A female patient approximately 65 years of age · a dermoscopic close-up of a skin lesion:
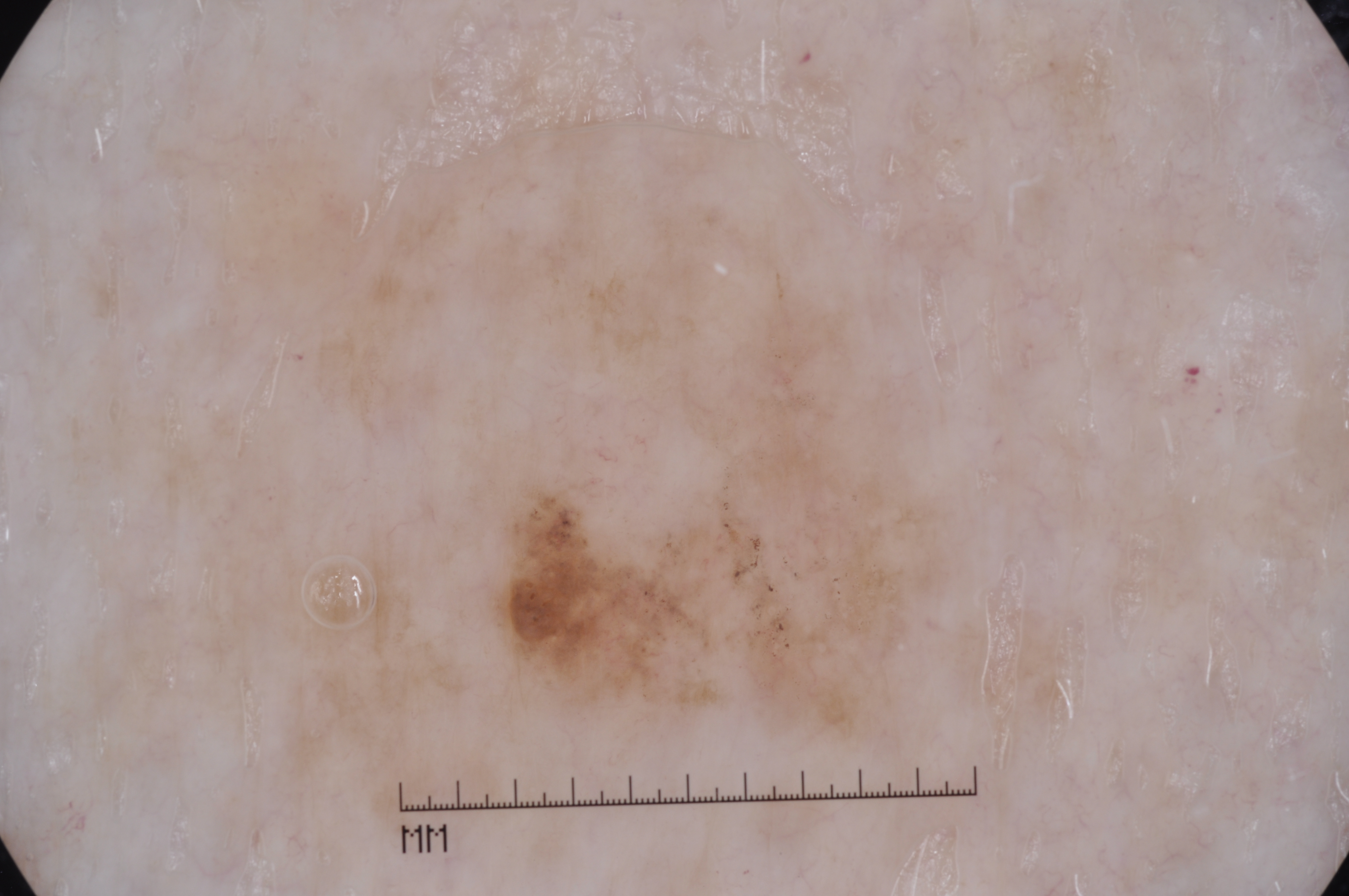Findings:
* features: milia-like cysts
* lesion bbox: 458/196/990/775
* extent: moderate
* assessment: a melanoma, a malignancy